A dermoscopic close-up of a skin lesion: 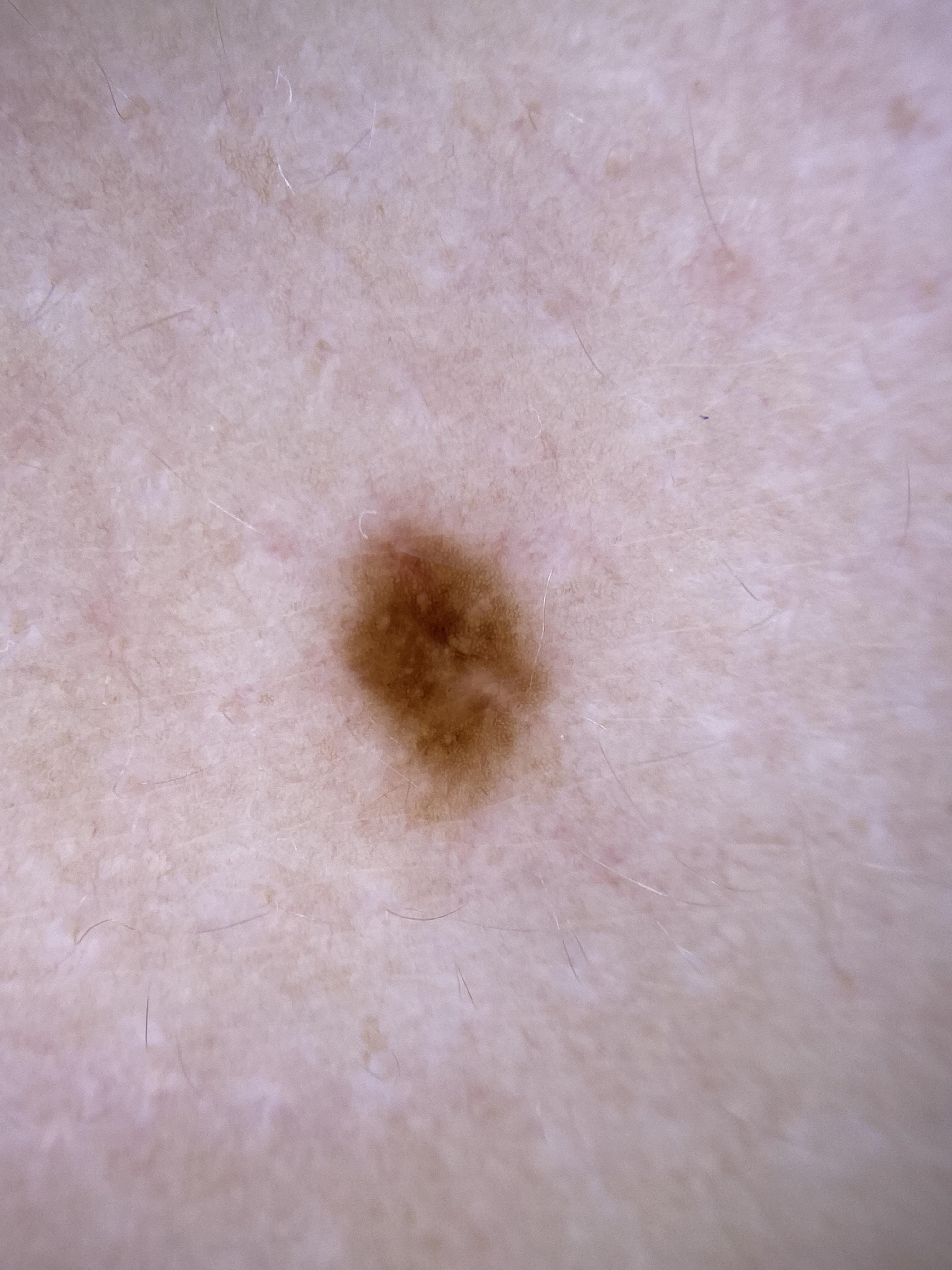{"lesion_location": {"region": "the trunk", "detail": "the posterior trunk"}, "diagnosis": {"name": "Nevus", "malignancy": "benign", "confirmation": "expert clinical impression", "lineage": "melanocytic"}}